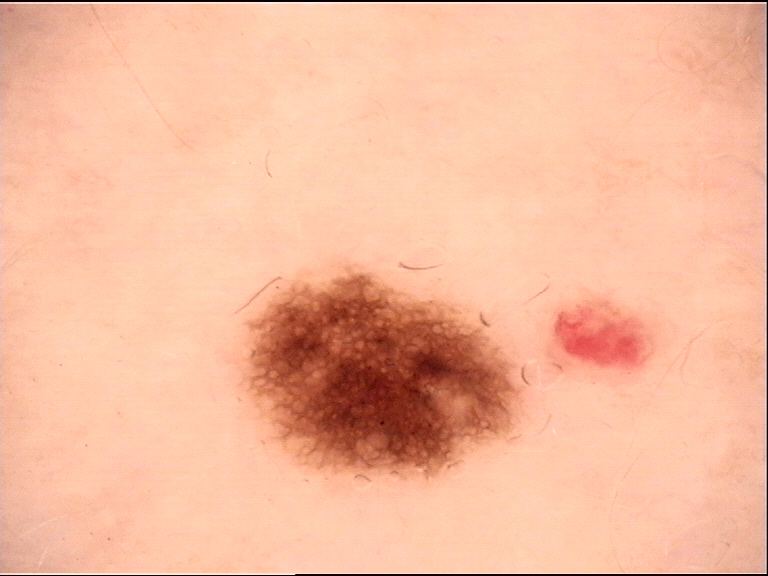assessment: dysplastic junctional nevus (expert consensus).